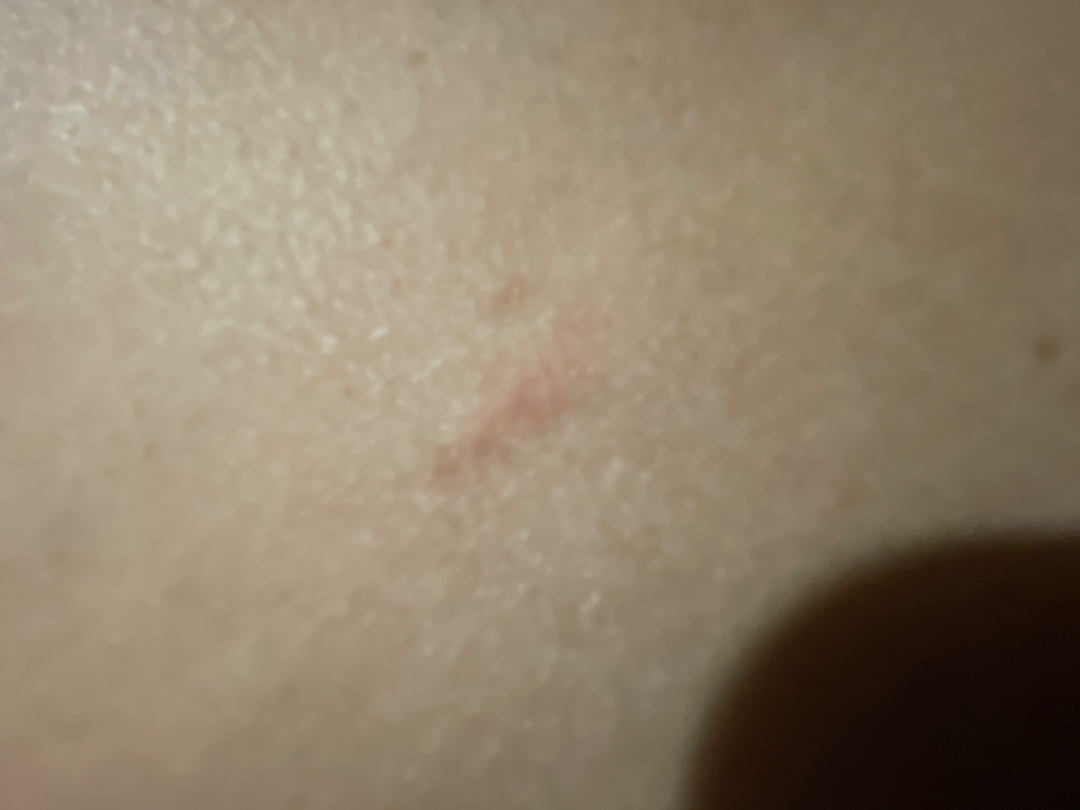Findings: The case was indeterminate on photographic review. Background: Close-up view.